Reported duration is one to four weeks. The patient considered this a rash. The patient notes pain, bothersome appearance, darkening, burning, bleeding, itching and enlargement. The lesion involves the palm and back of the hand. This image was taken at an angle. Texture is reported as fluid-filled:
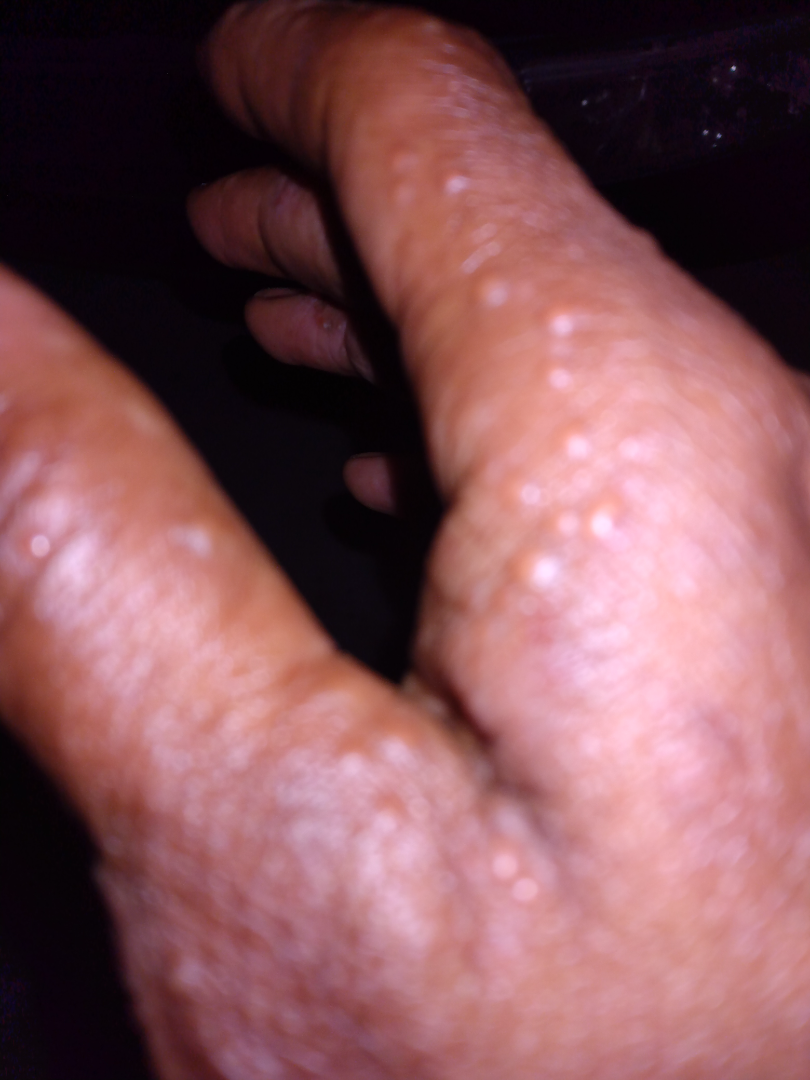* differential — Eczema (0.28); Acral persistent papular mucinosis (0.22); Cutaneous sarcoidosis (0.22); Allergic Contact Dermatitis (0.17); Verruca vulgaris (0.11)